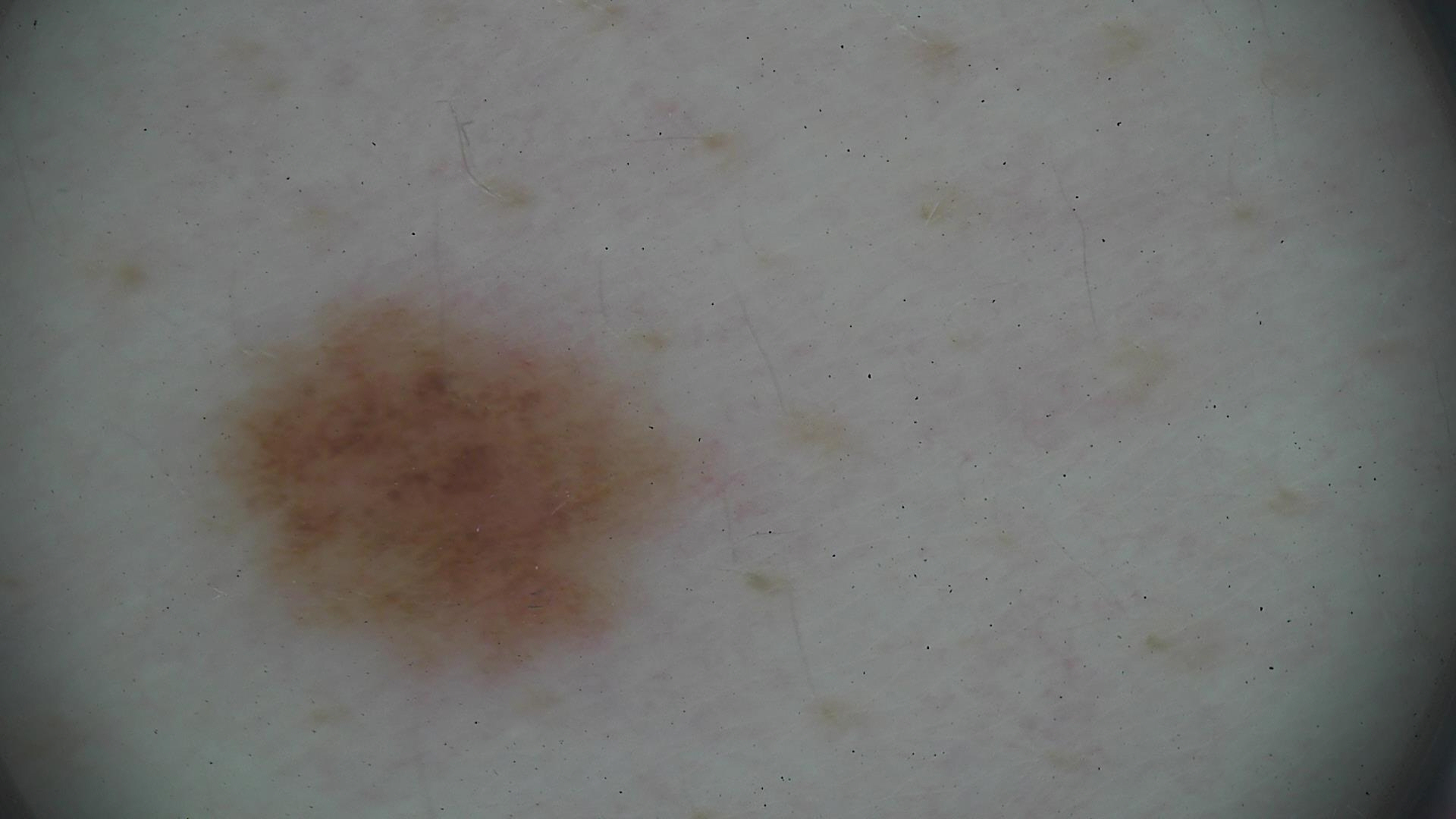Impression: Classified as a dysplastic junctional nevus.